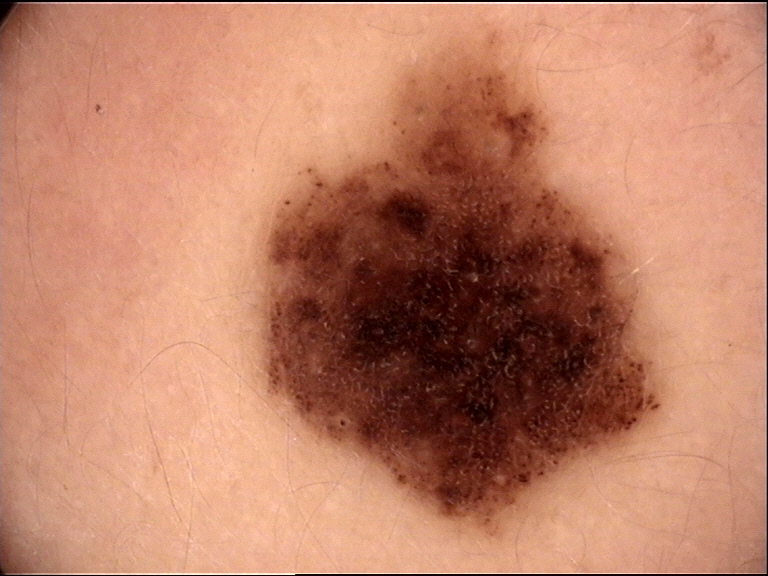class: dysplastic compound nevus (expert consensus)